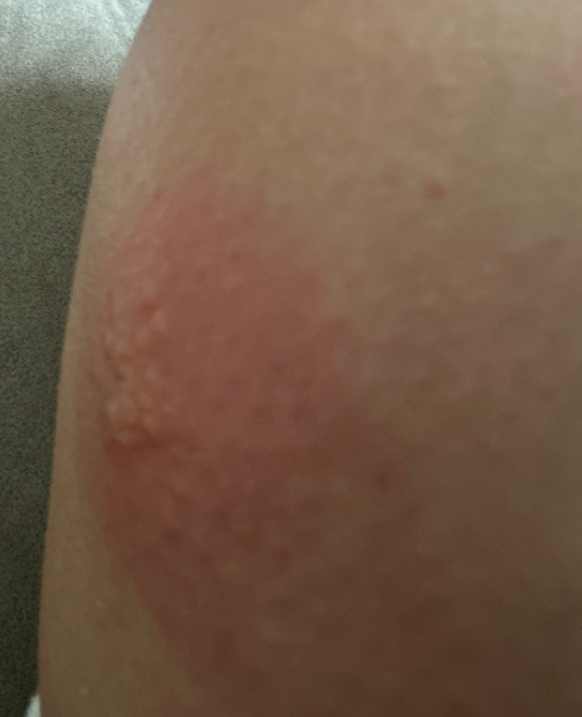{"differential": {"leading": ["Herpes Simplex"]}}